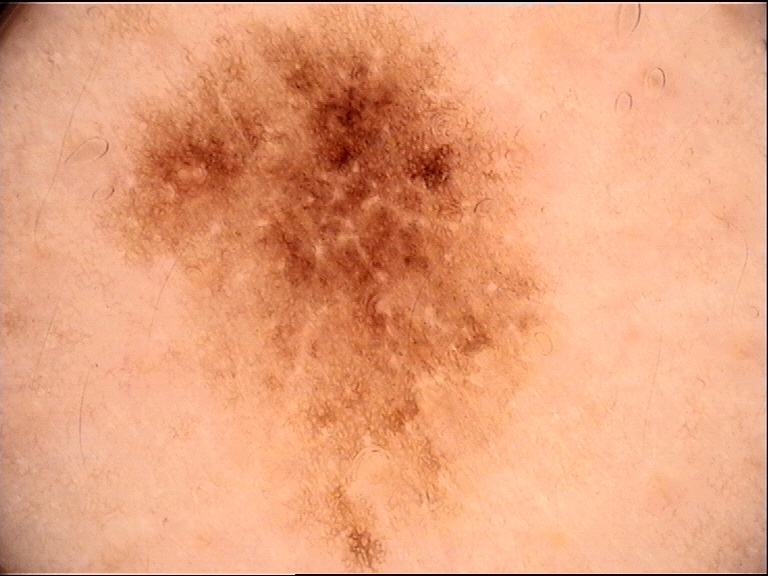Dermoscopy of a skin lesion. The diagnostic label was a benign lesion — a dysplastic junctional nevus.